A clinical close-up photograph of a skin lesion. A patient in their mid-50s — 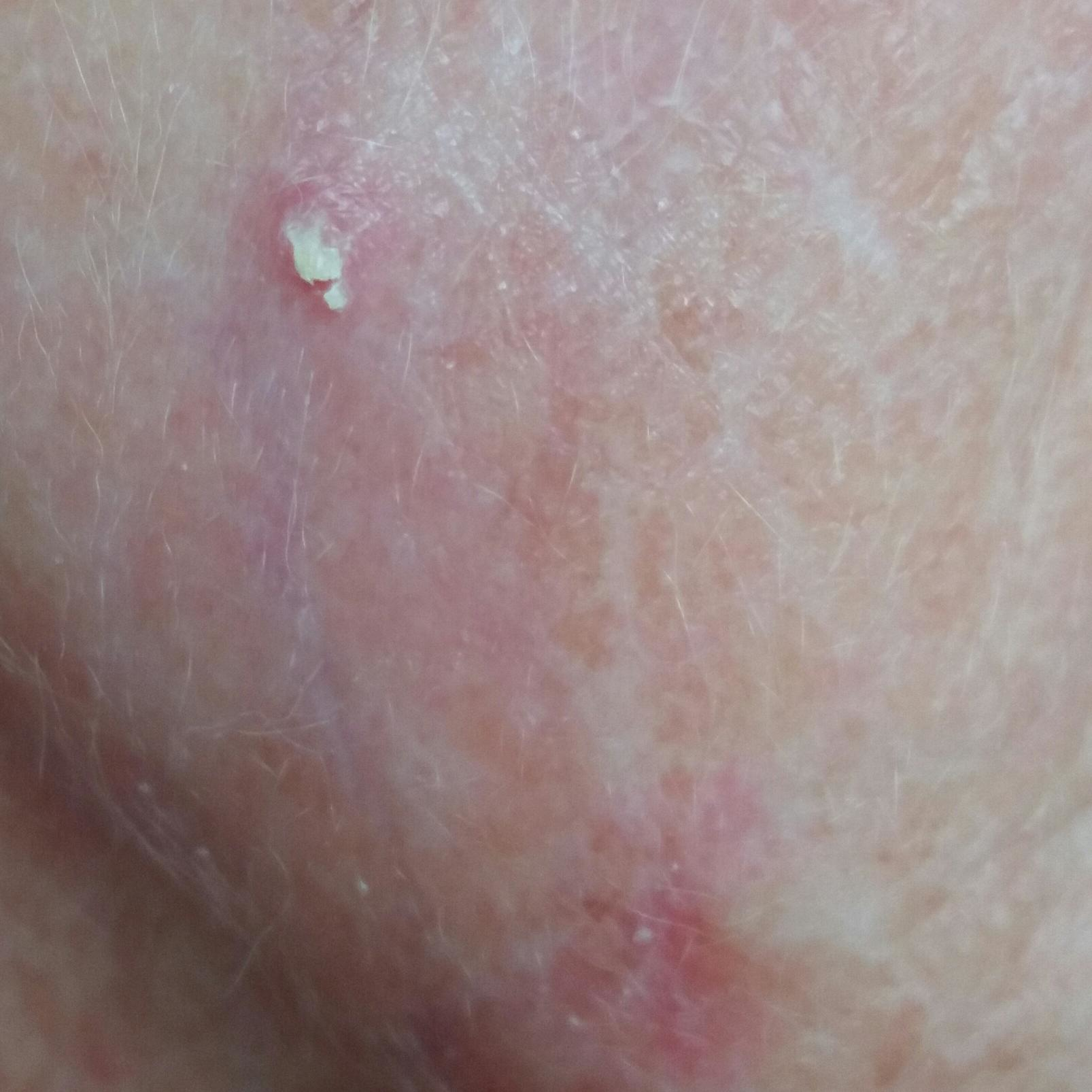reported symptoms: elevation, itching; diagnosis: actinic keratosis (clinical consensus).